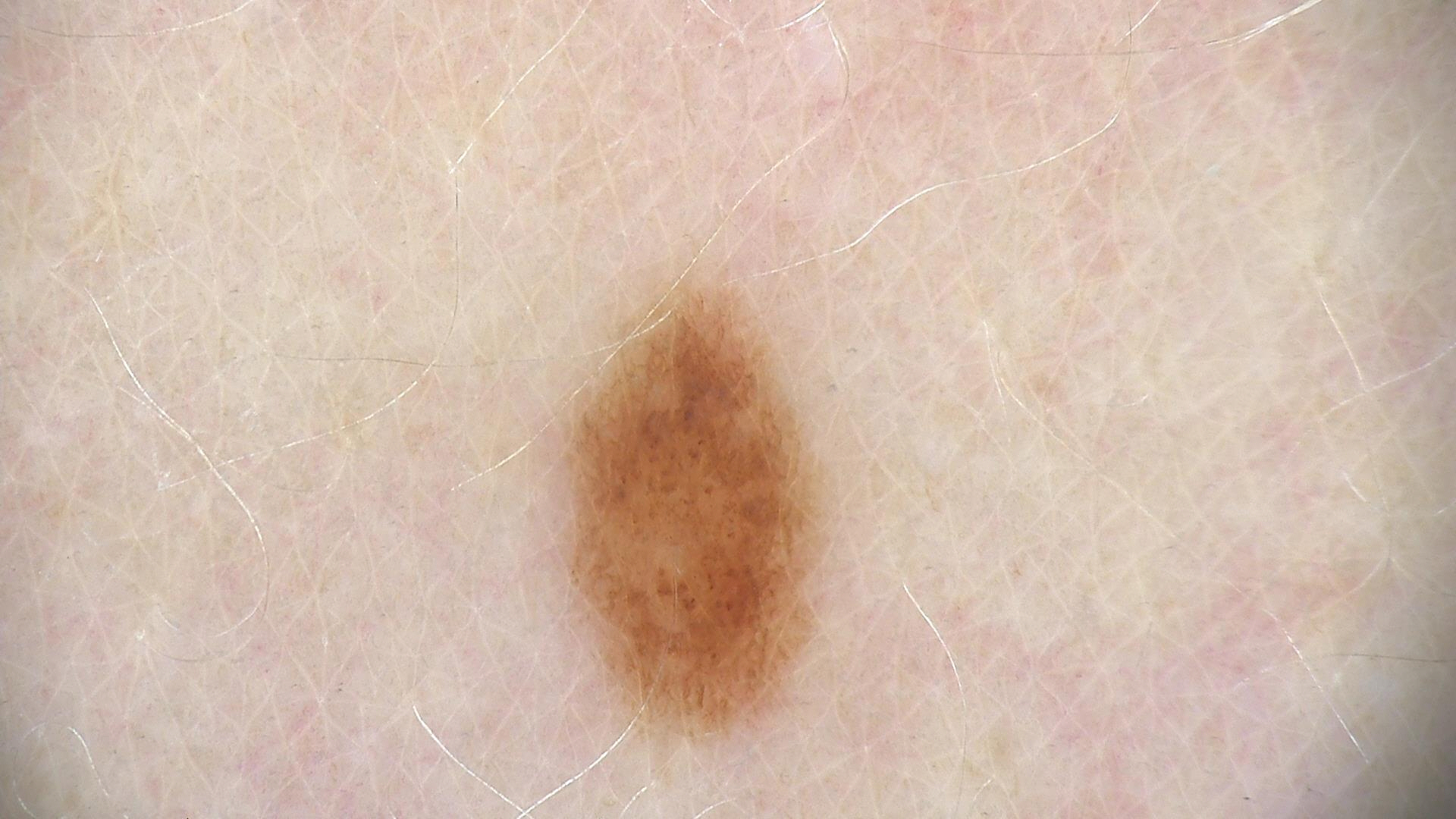A dermoscopic image of a skin lesion.
Diagnosed as a benign lesion — a dysplastic junctional nevus.